A dermoscopic photograph of a skin lesion.
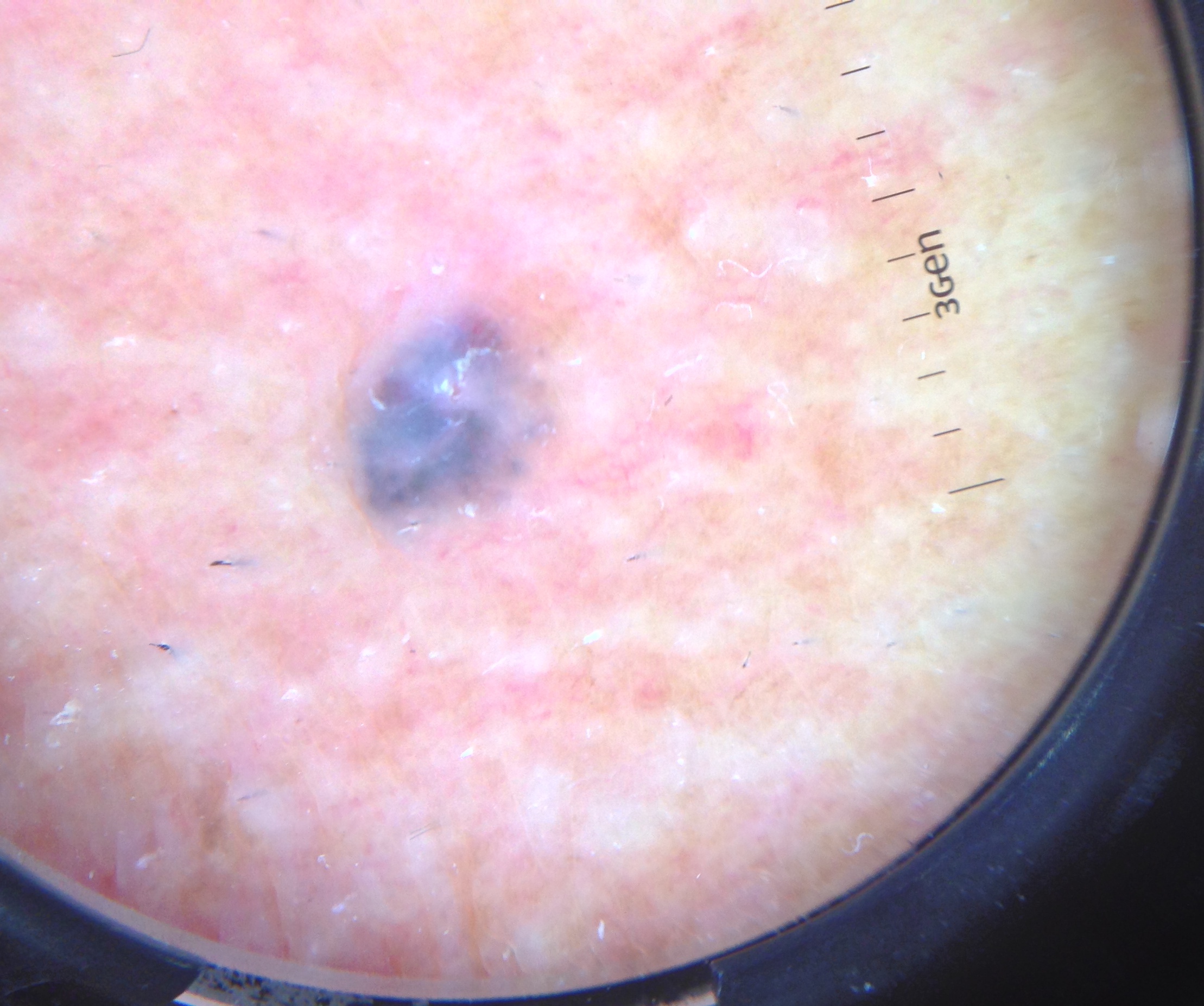The biopsy diagnosis was a basal cell carcinoma.